An image taken at an angle; the lesion involves the leg.
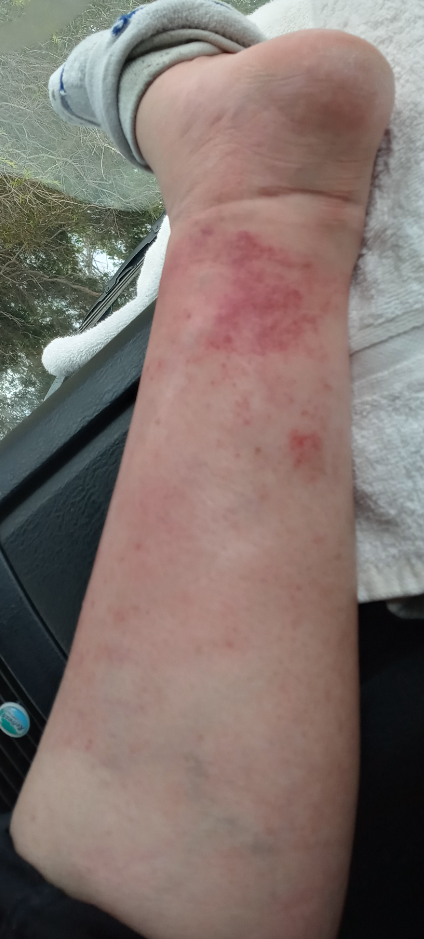The lesion is associated with burning, bothersome appearance, pain, enlargement and darkening.
The lesion is described as raised or bumpy.
The patient indicates the condition has been present for one to four weeks.
The patient indicates associated joint pain.
On remote review of the image: the favored diagnosis is Stasis Dermatitis; with consideration of Pigmented purpuric eruption; less likely is Eczema.